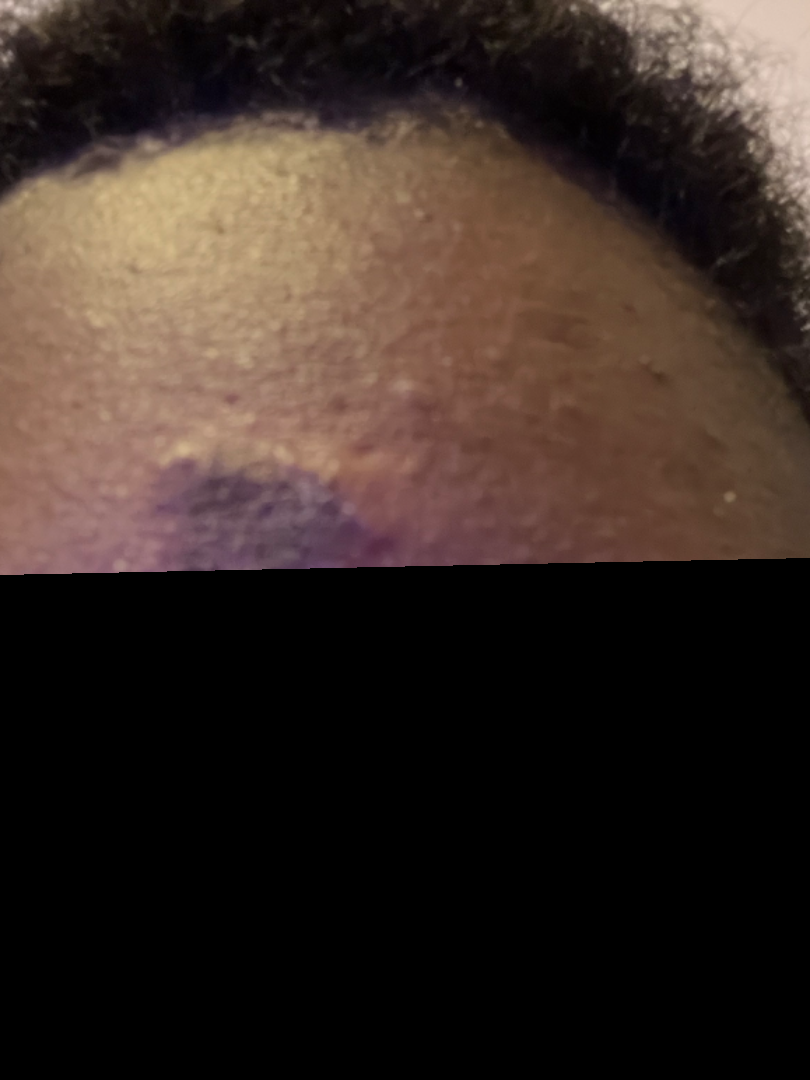The skin findings could not be characterized from the image. Female subject, age 18–29. This is a close-up image. The affected area is the head or neck.